Reported duration is more than five years, symptoms reported: bothersome appearance and enlargement, the sole of the foot is involved, the patient described the issue as a rash, the photograph was taken at a distance, no constitutional symptoms were reported:
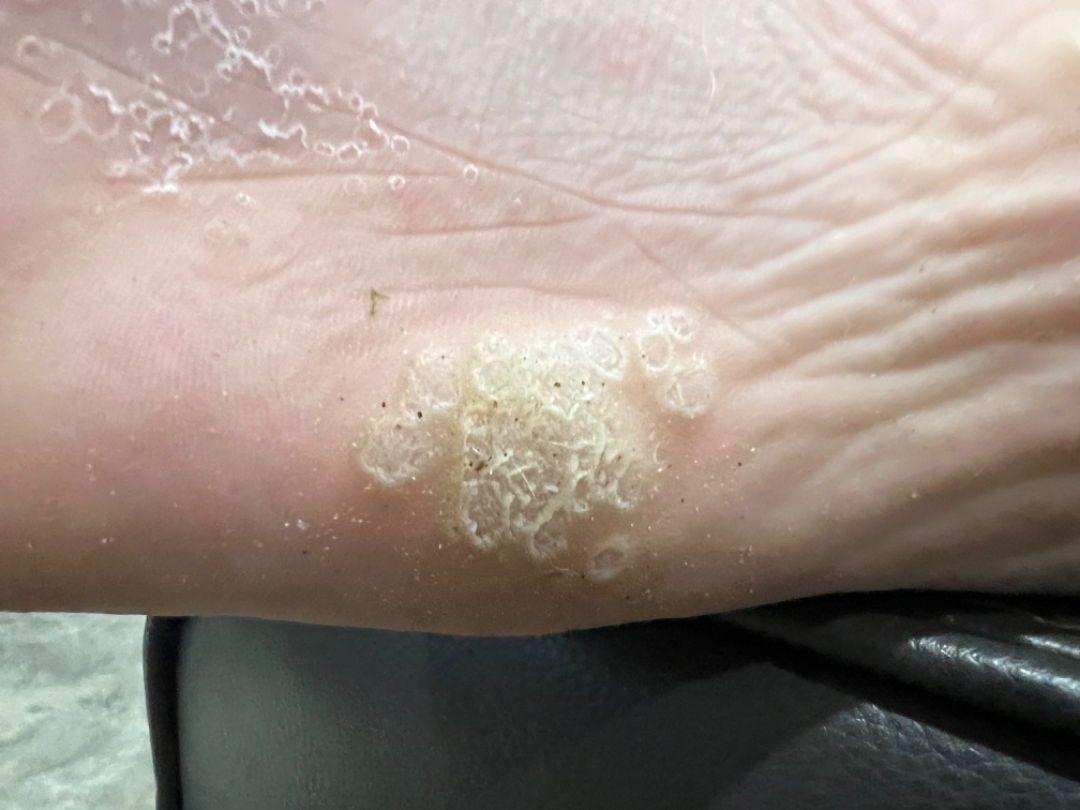Assessment: Consistent with Verruca vulgaris.